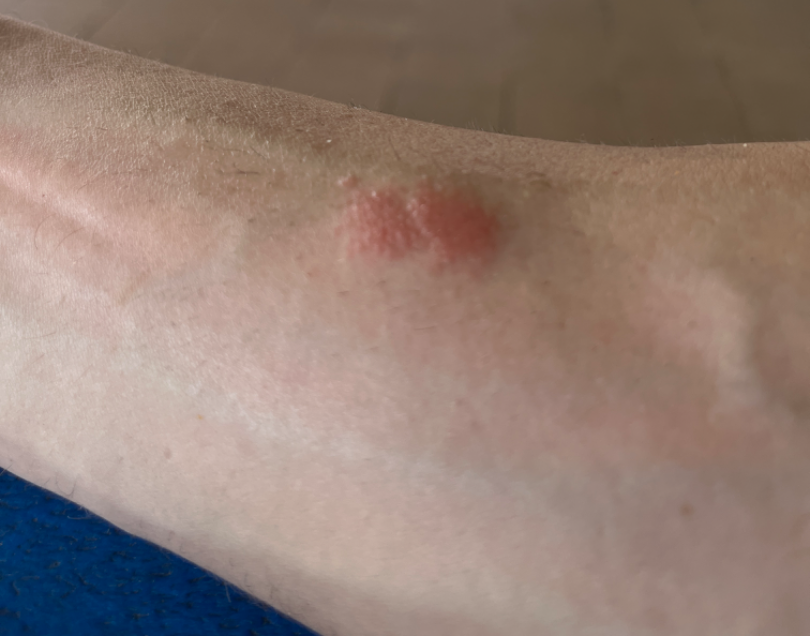| field | value |
|---|---|
| assessment | ungradable on photographic review |
| subject | male, age 18–29 |
| lesion texture | raised or bumpy |
| anatomic site | arm |
| shot type | at an angle |
| present for | one to four weeks |
| patient's own categorization | a rash |